The photo was captured at a distance — 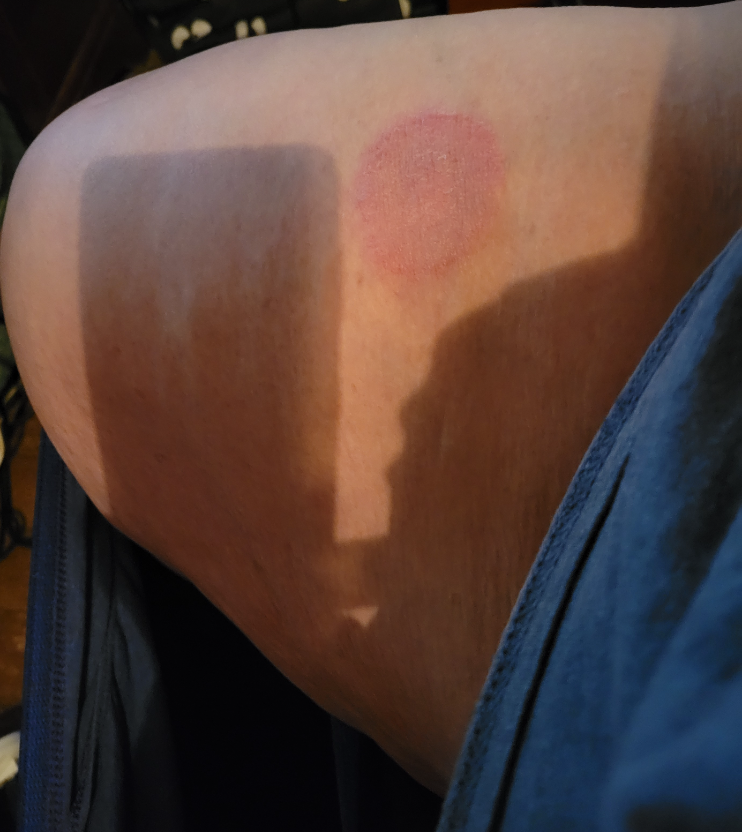Q: What conditions are considered?
A: one reviewing dermatologist: most consistent with Tinea; an alternative is Eczema